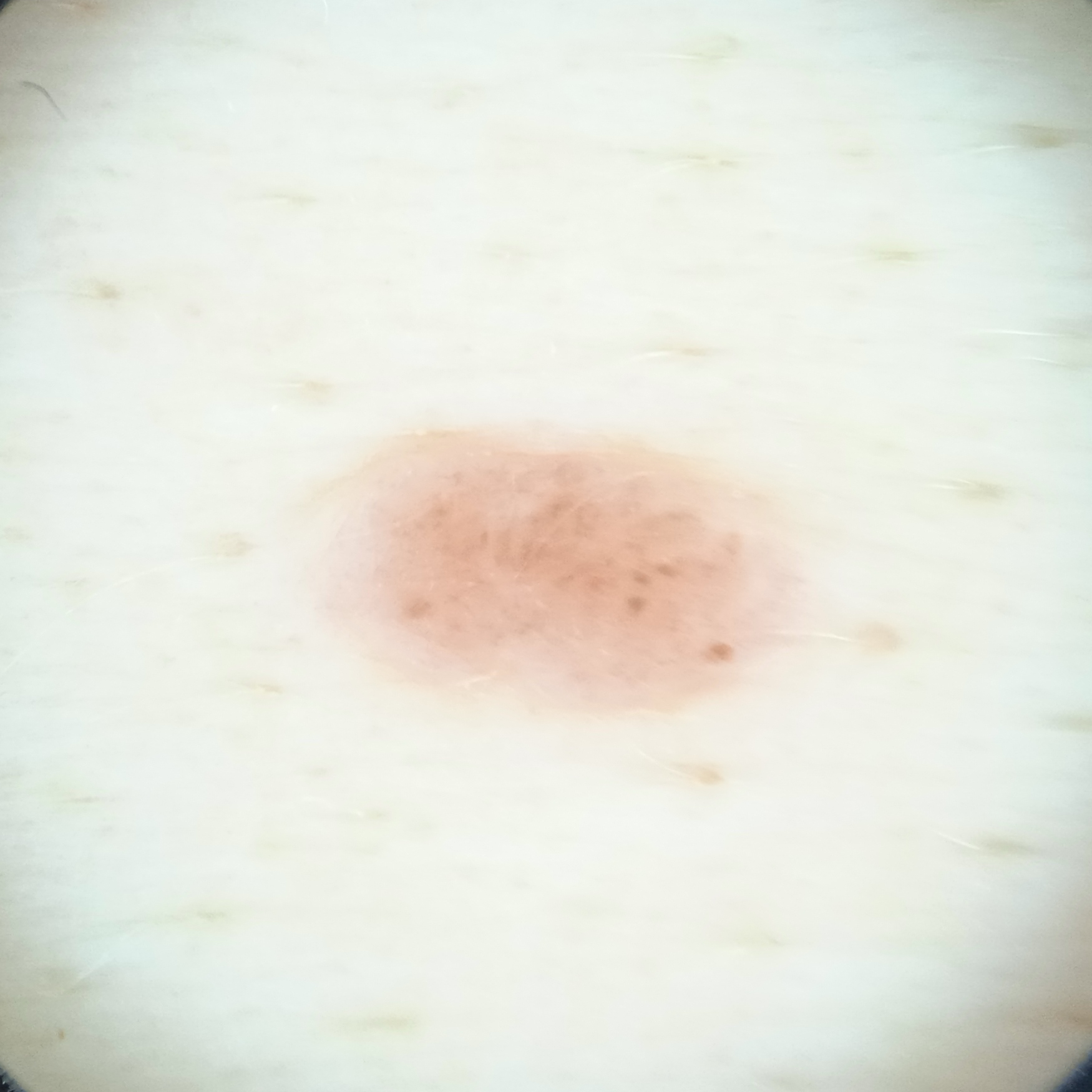nevus count: a moderate number of melanocytic nevi
image type: dermoscopy
patient: female, aged 50
anatomic site: the torso
diagnosis: melanocytic nevus (dermatologist consensus)